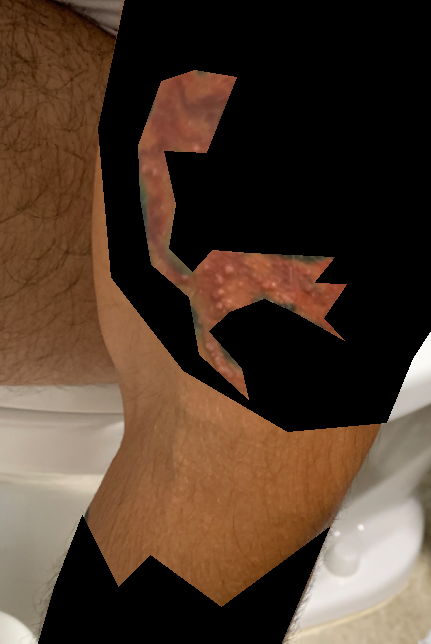The photo was captured at a distance. The affected area is the arm. The patient is 18–29, male. The lesion is associated with bothersome appearance and itching. Self-categorized by the patient as a rash. The reviewing panel's impression was: the favored diagnosis is Skin infection; also raised was Foreign body reaction of the skin.